A female patient aged 28-32 · a dermoscopic close-up of a skin lesion — 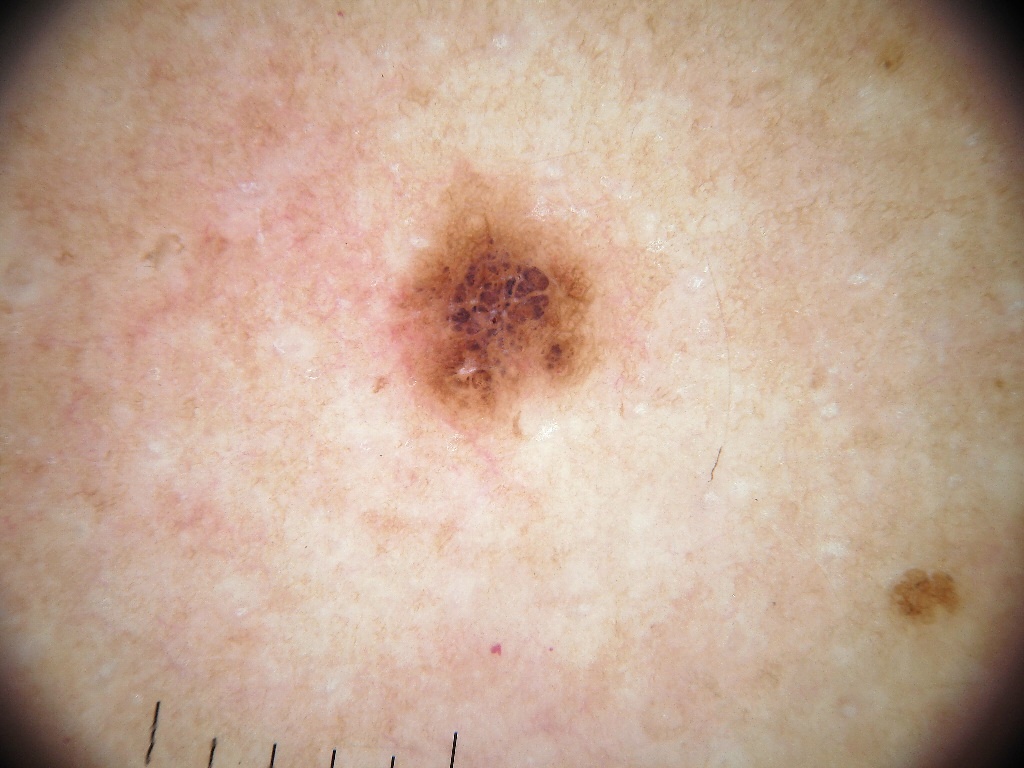Summary:
The lesion covers approximately 4% of the dermoscopic field. As (left, top, right, bottom), lesion location: box(387, 167, 598, 421). Dermoscopically, the lesion shows pigment network.
Conclusion:
The diagnostic assessment was a melanocytic nevus, a benign lesion.